A dermoscopic photograph of a skin lesion: 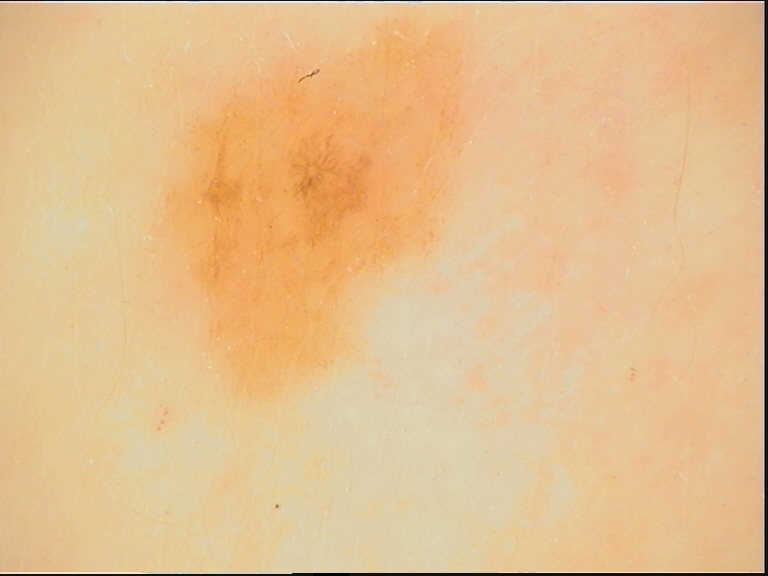Consistent with a junctional nevus.